Dermoscopy of a skin lesion: 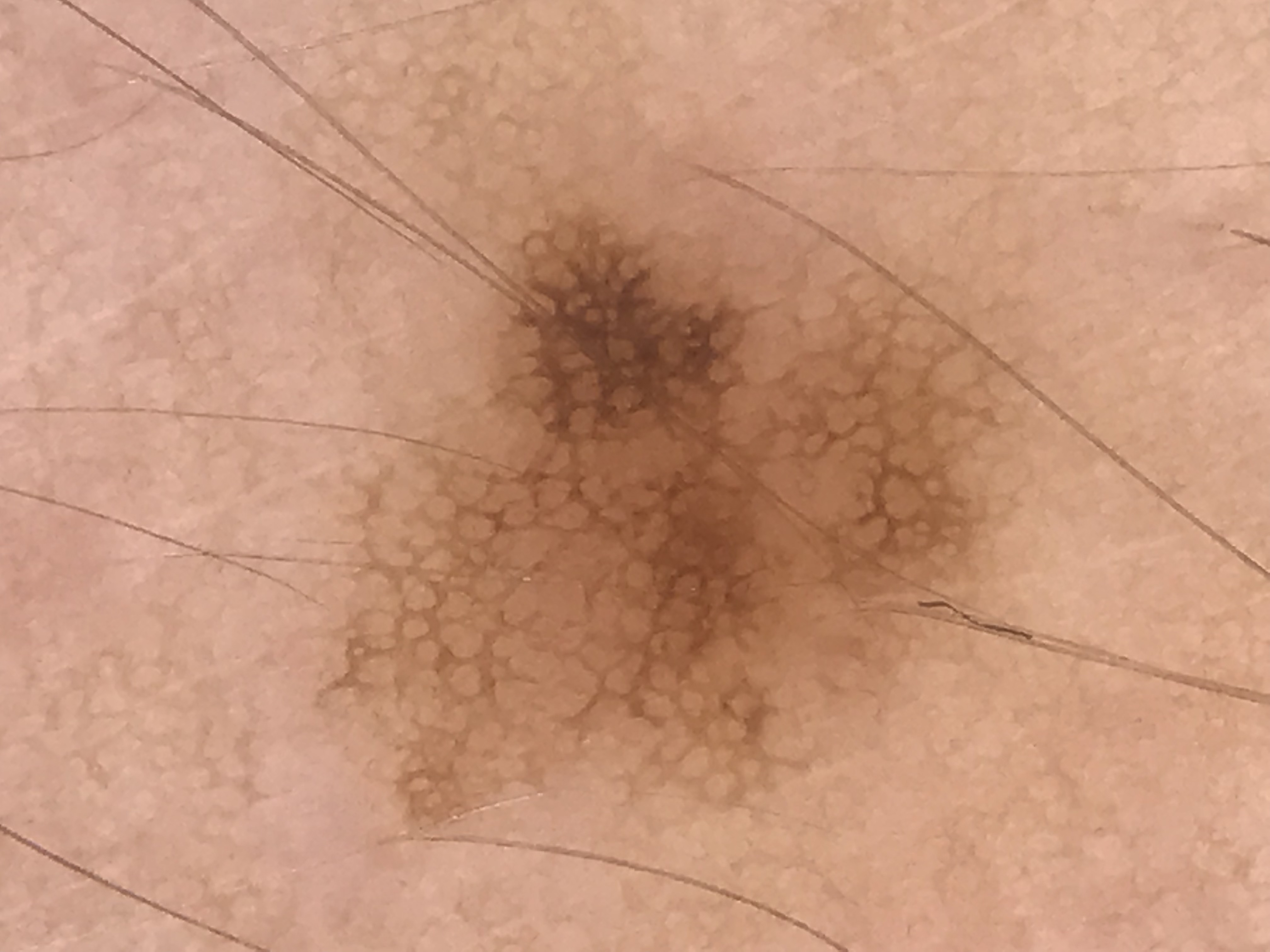{"diagnosis": {"name": "dysplastic junctional nevus", "code": "jd", "malignancy": "benign", "super_class": "melanocytic", "confirmation": "expert consensus"}}